A dermoscopy image of a single skin lesion.
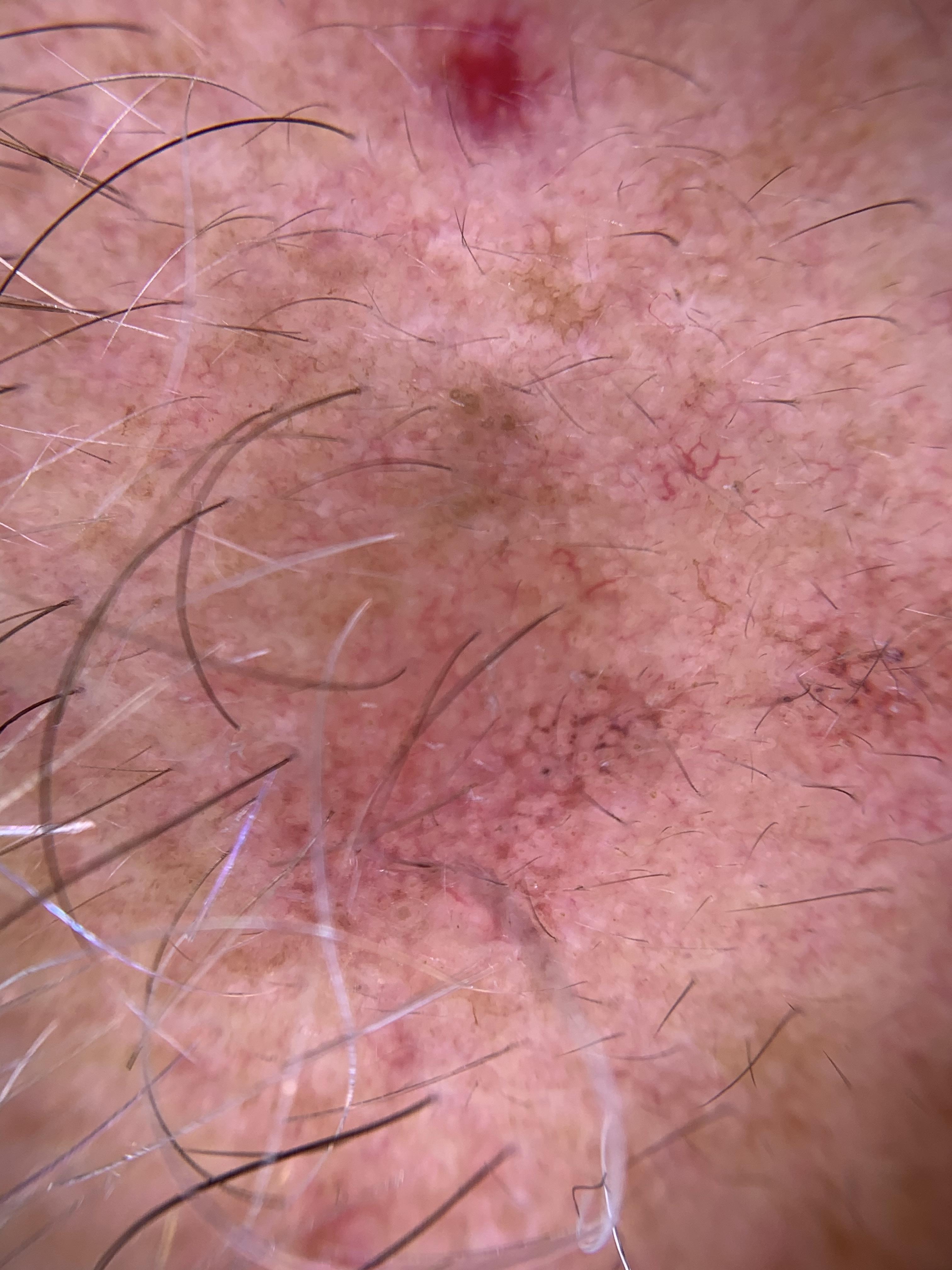anatomic site=the head or neck; diagnostic label=Solar or actinic keratosis (clinical impression).